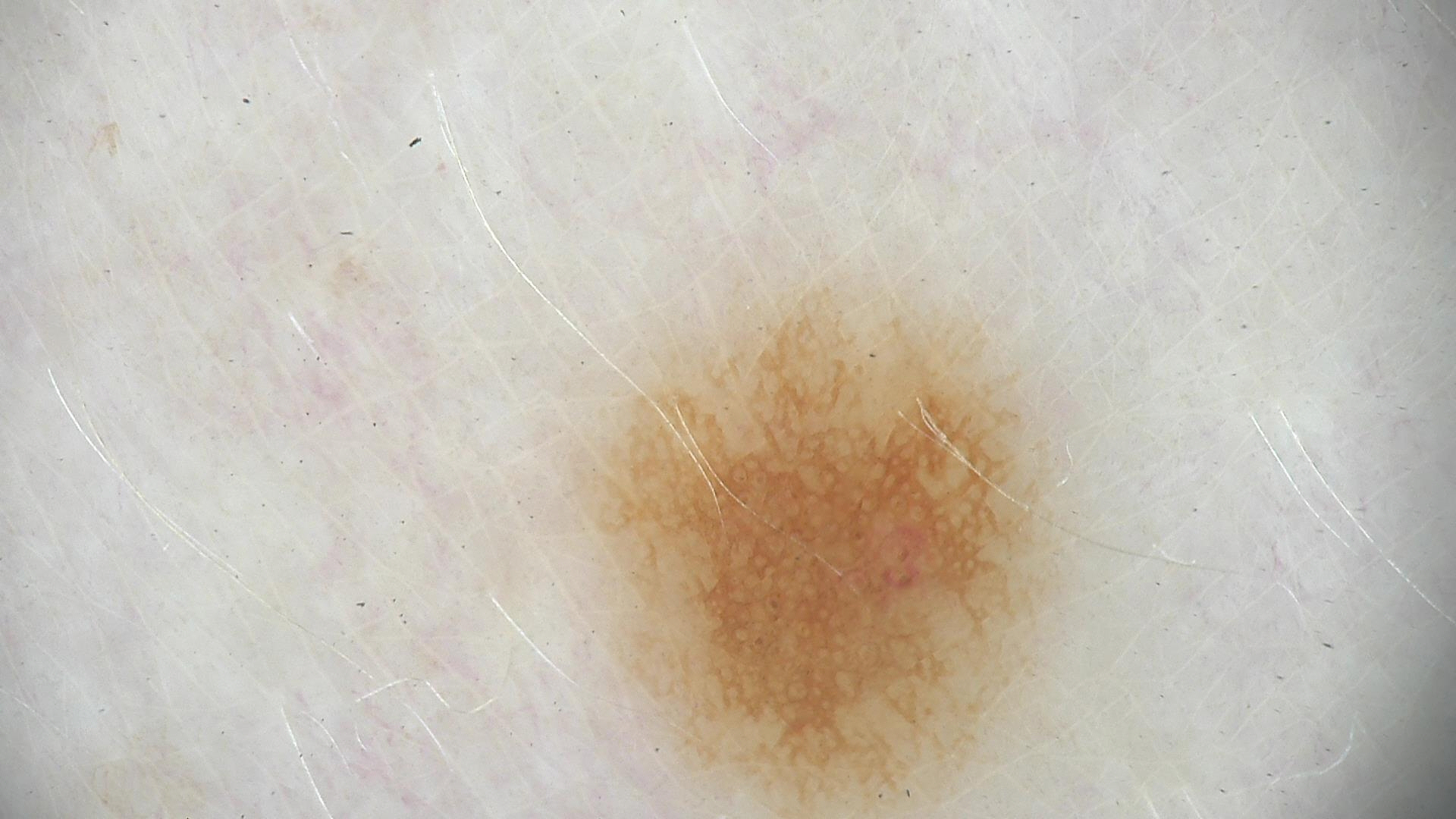Findings: Dermoscopy of a skin lesion. Impression: The diagnosis was a dysplastic junctional nevus.